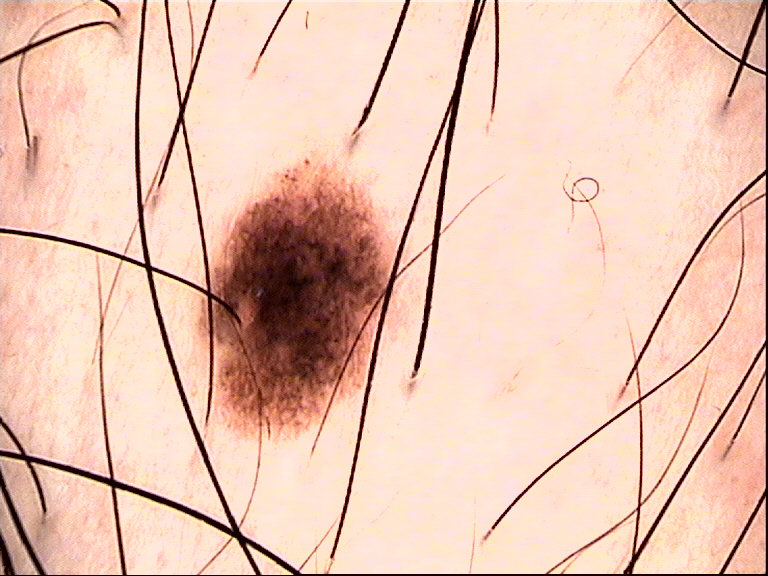assessment = dysplastic compound nevus (expert consensus).